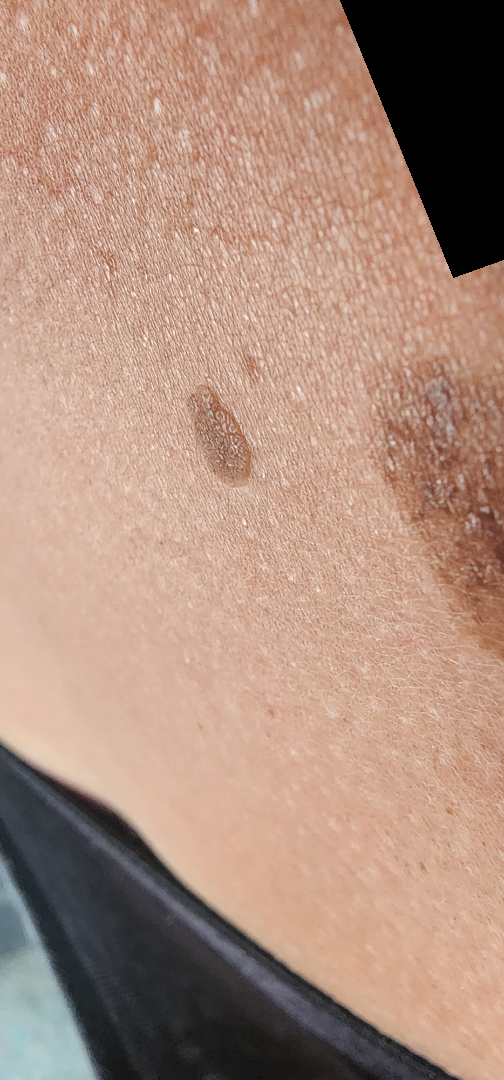Case summary:
• shot type · at an angle
• anatomic site · back of the torso
• symptoms · bothersome appearance
• lesion texture · raised or bumpy
• patient describes the issue as · a growth or mole
• assessment · SK/ISK (55%); Melanocytic Nevus (27%); Actinic Keratosis (18%)